A dermoscopic photograph of a skin lesion.
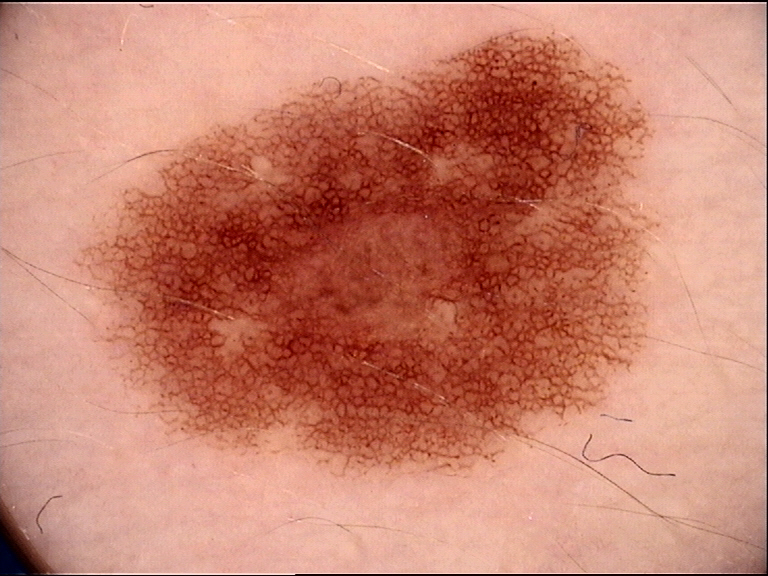Classified as a dysplastic compound nevus.